The affected area is the front of the torso. The contributor is a female aged 18–29. The photograph is a close-up of the affected area — 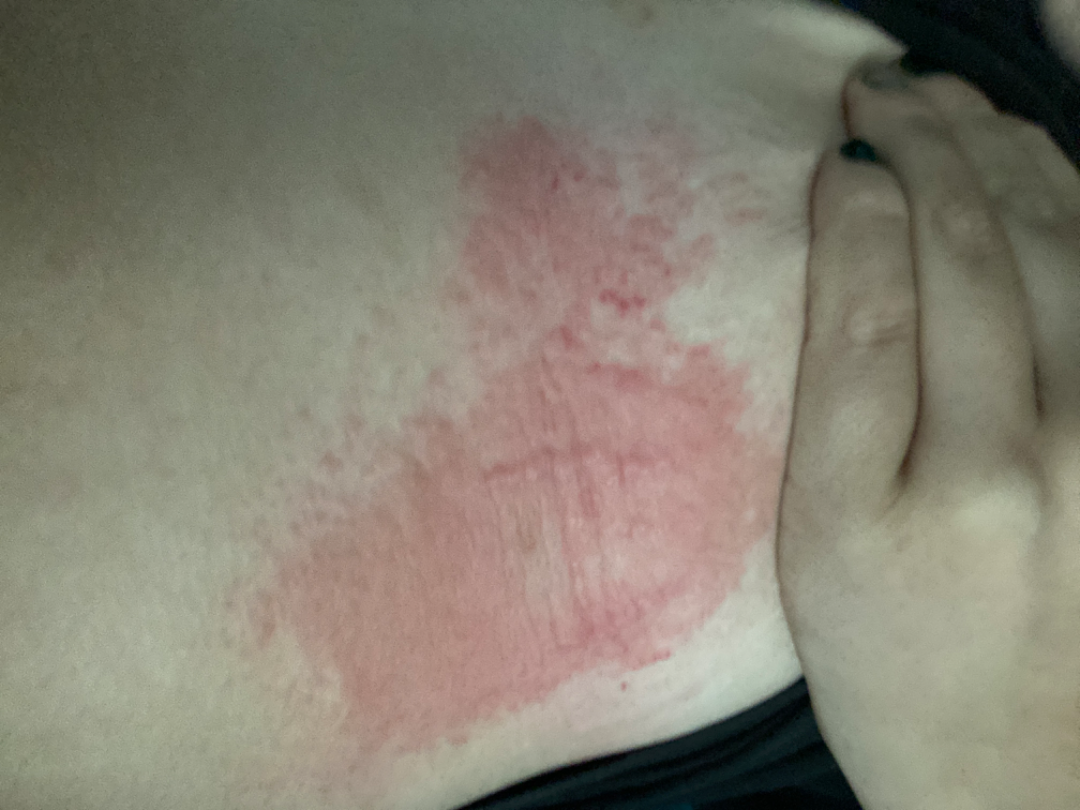Q: Reported symptoms?
A: darkening, burning, bothersome appearance, enlargement and itching
Q: What conditions are considered?
A: the favored diagnosis is Allergic Contact Dermatitis; less likely is Acute dermatitis, NOS; a more distant consideration is Cellulitis; lower on the differential is Tinea; less probable is Eczema; a remote consideration is Urticarial vasculitis